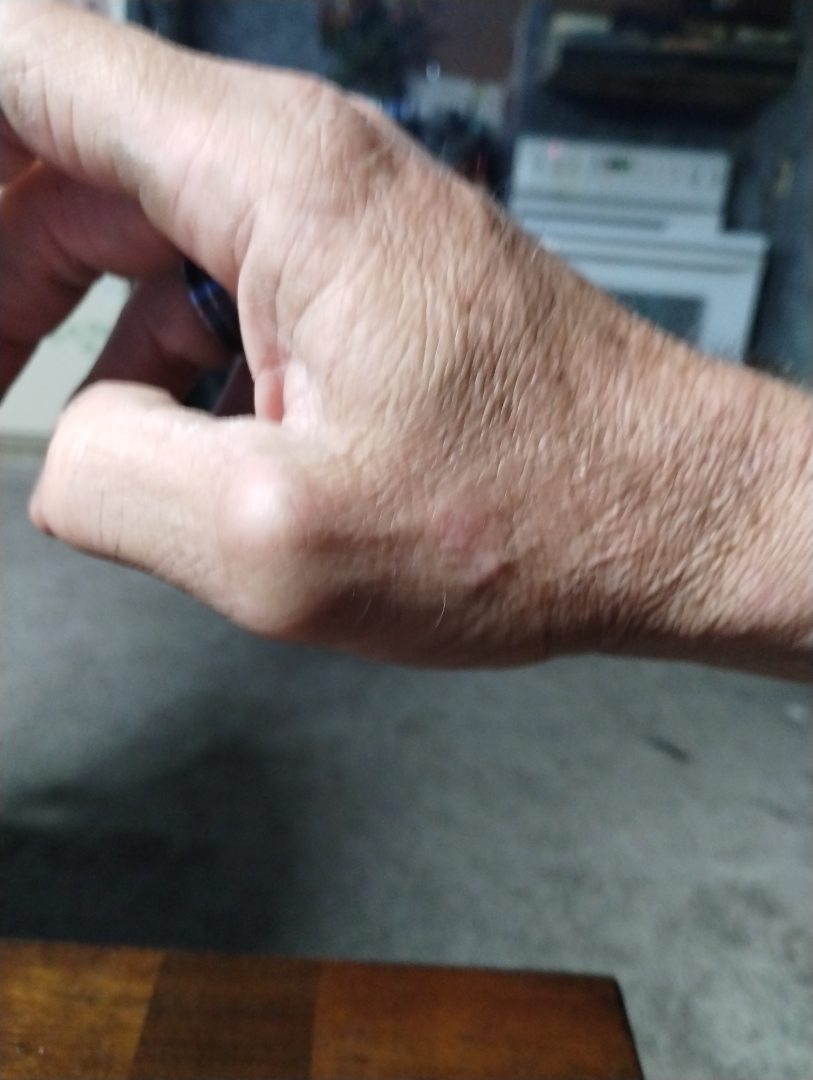  assessment: indeterminate from the photograph
  shot_type: close-up